The patient describes having a moderate number of moles · a female patient 47 years old · collected as part of a research study, without a referral diagnosis — 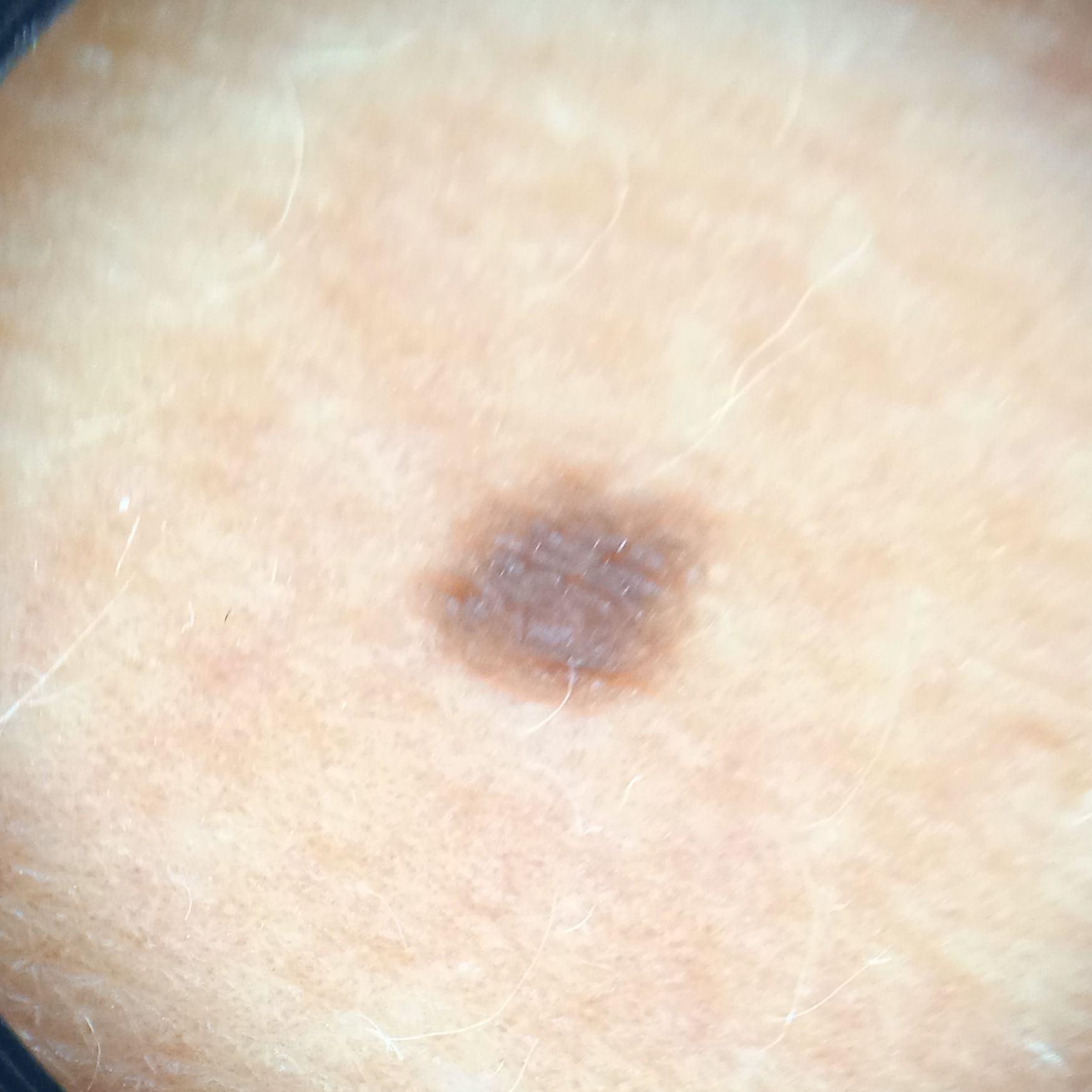anatomic site = an arm, diagnosis = melanocytic nevus (dermatologist consensus).